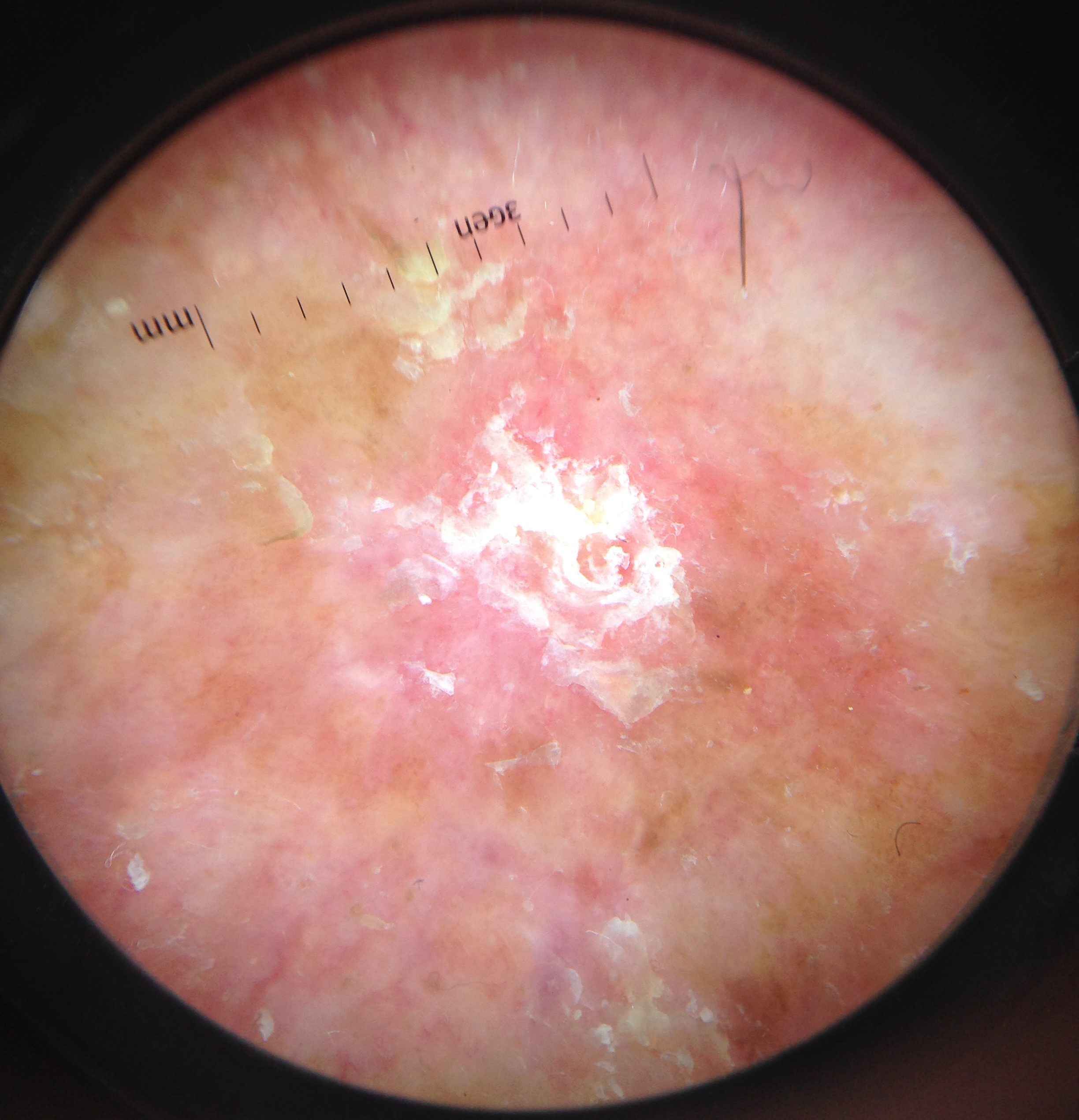Biopsy-confirmed as a squamous cell carcinoma.